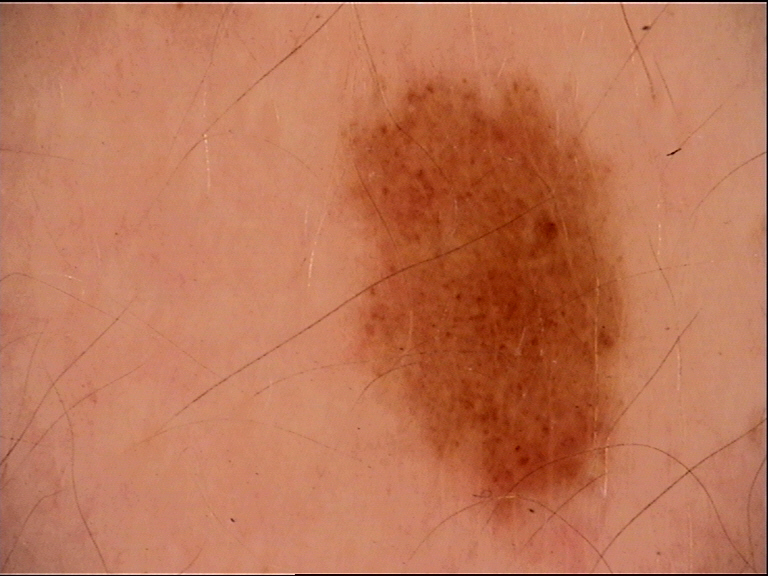A dermoscopic close-up of a skin lesion.
The diagnostic label was a dysplastic junctional nevus.